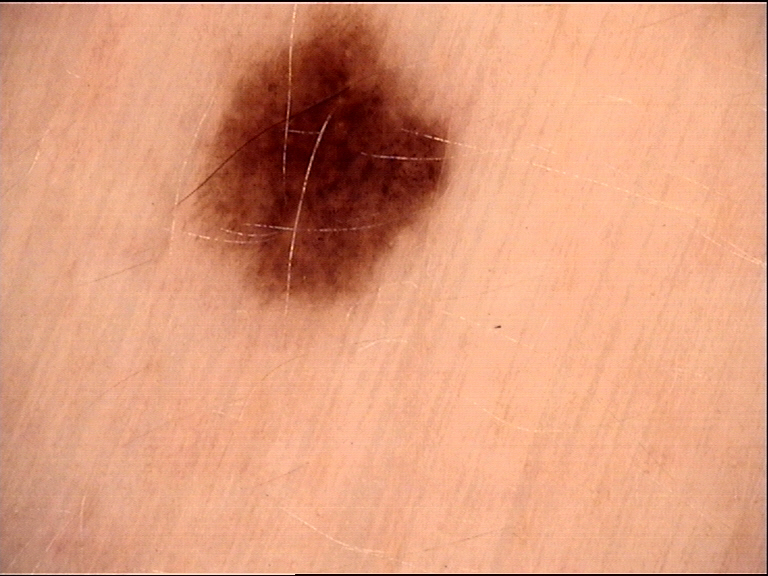class: dysplastic junctional nevus (expert consensus).